The subject is a female about 40 years old, a skin lesion imaged with a dermatoscope.
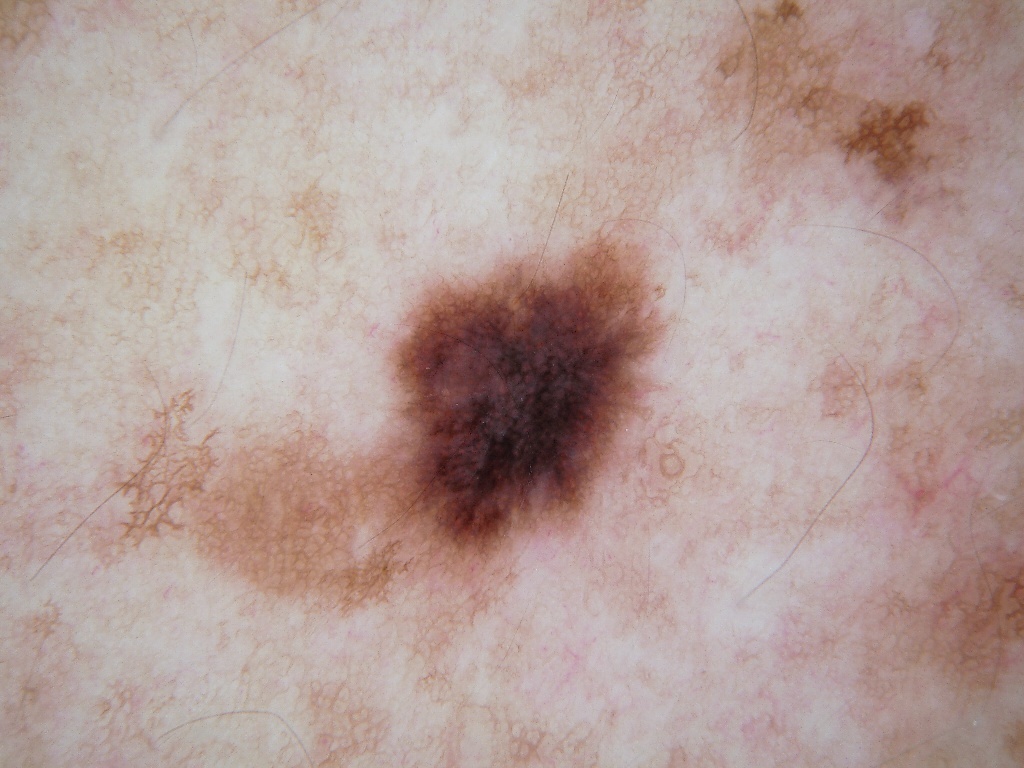| key | value |
|---|---|
| dermoscopic findings | pigment network; absent: streaks, globules, negative network, and milia-like cysts |
| extent | ~12% of the field |
| lesion location | x1=370, y1=210, x2=675, y2=592 |
| impression | a melanocytic nevus |